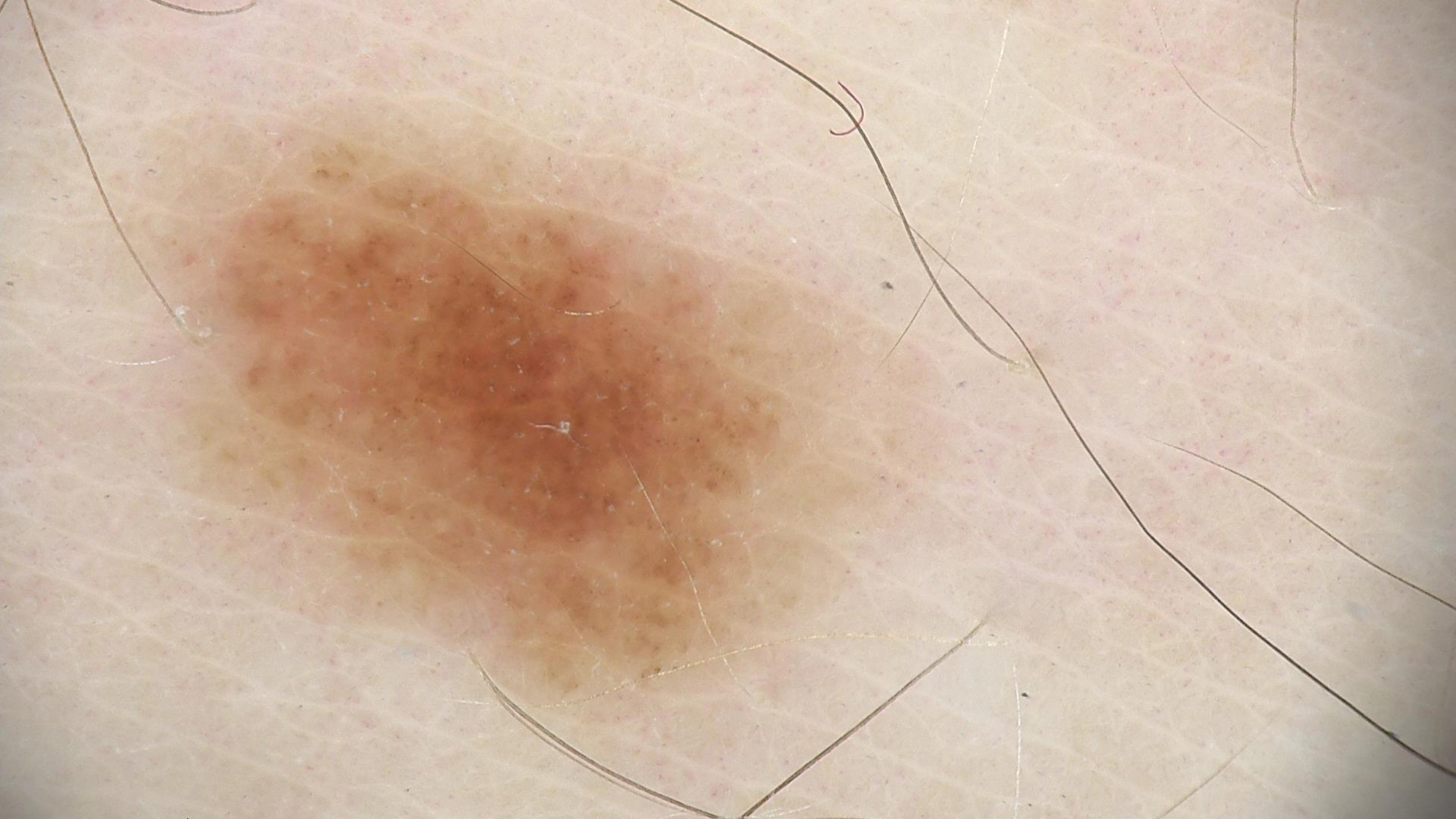Classified as a dysplastic junctional nevus.